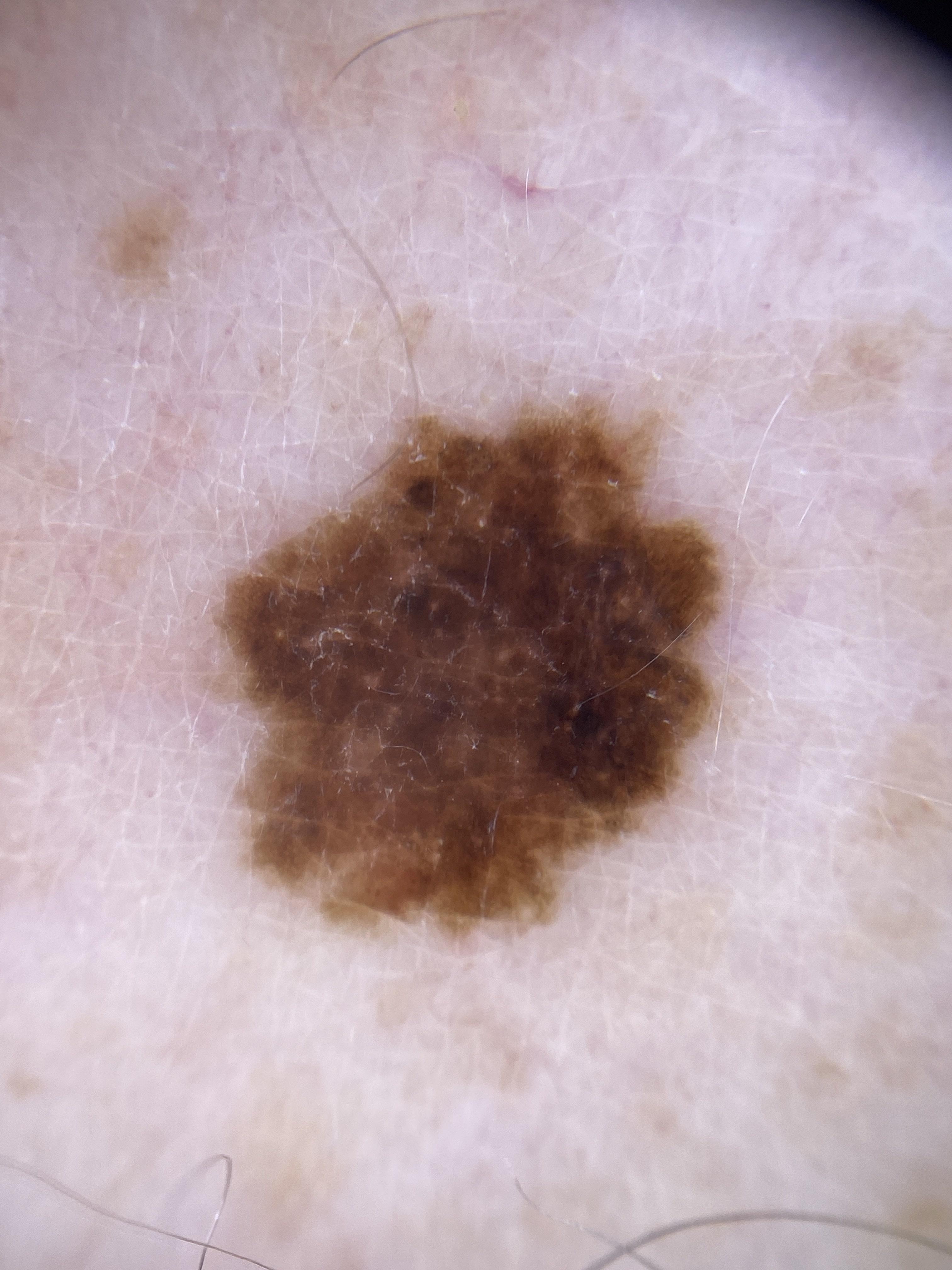- relevant background · a previous melanoma but no melanoma in first-degree relatives
- diagnosis · Nevus (biopsy-proven)